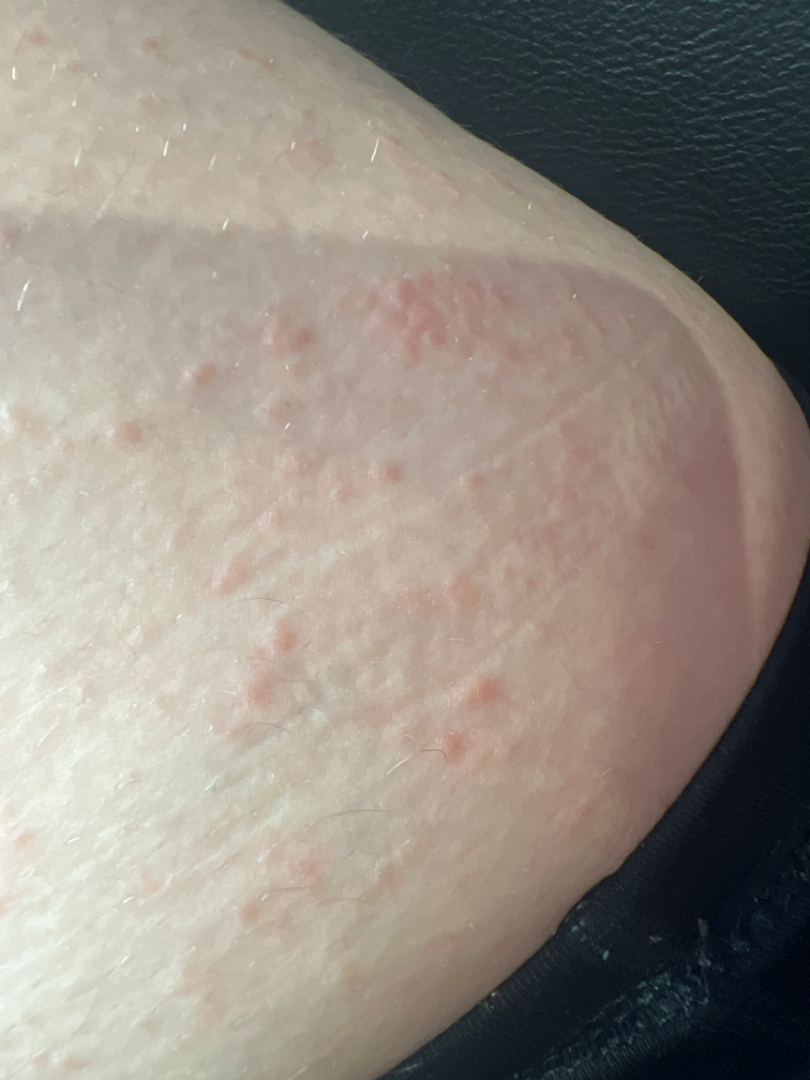Q: Could the case be diagnosed?
A: could not be assessed
Q: Who is the patient?
A: female, age 18–29
Q: What is the affected area?
A: leg
Q: Image view?
A: close-up